The photograph is a close-up of the affected area, the contributor is a female aged 70–79, located on the front of the torso:
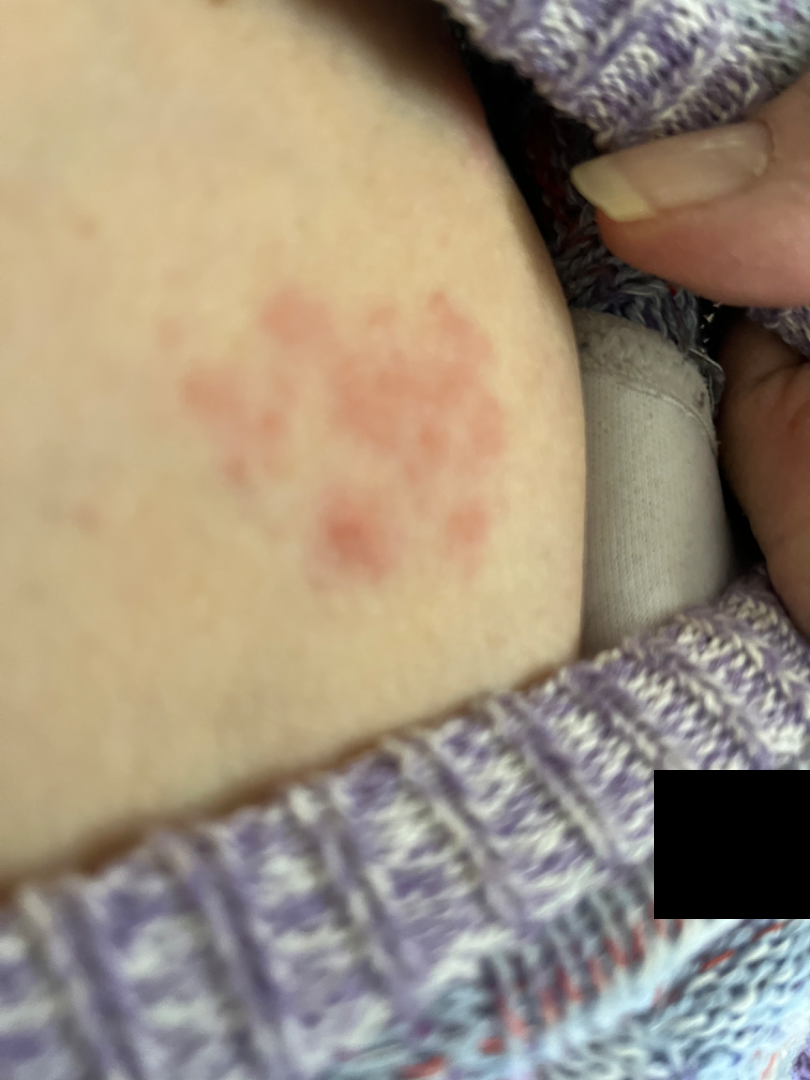Findings:
• lesion texture — raised or bumpy
• history — about one day
• self-categorized as — a rash
• diagnostic considerations — a single dermatologist reviewed the case: the differential is split between Insect Bite, Allergic Contact Dermatitis and Herpes Simplex